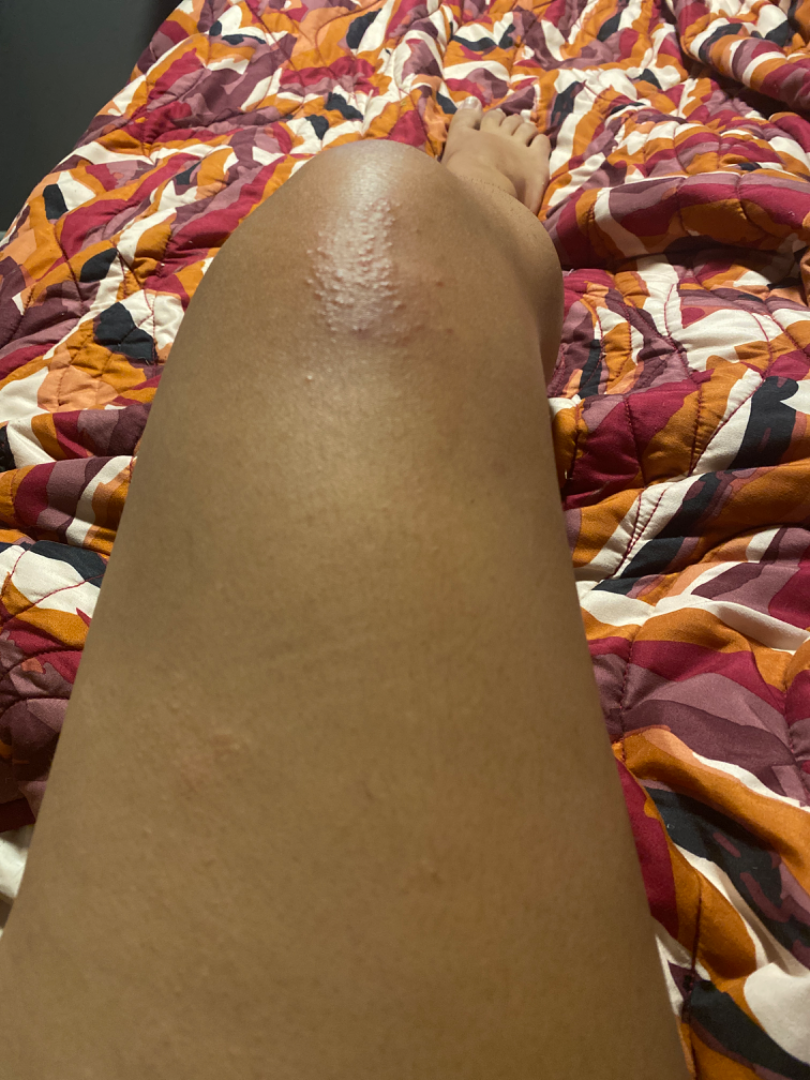History: The photo was captured at a distance. The contributor is a female aged 18–29. The lesion involves the leg. Impression: Favoring Lichen spinulosus; also on the differential is Keratosis pilaris; less probable is Lichen nitidus.